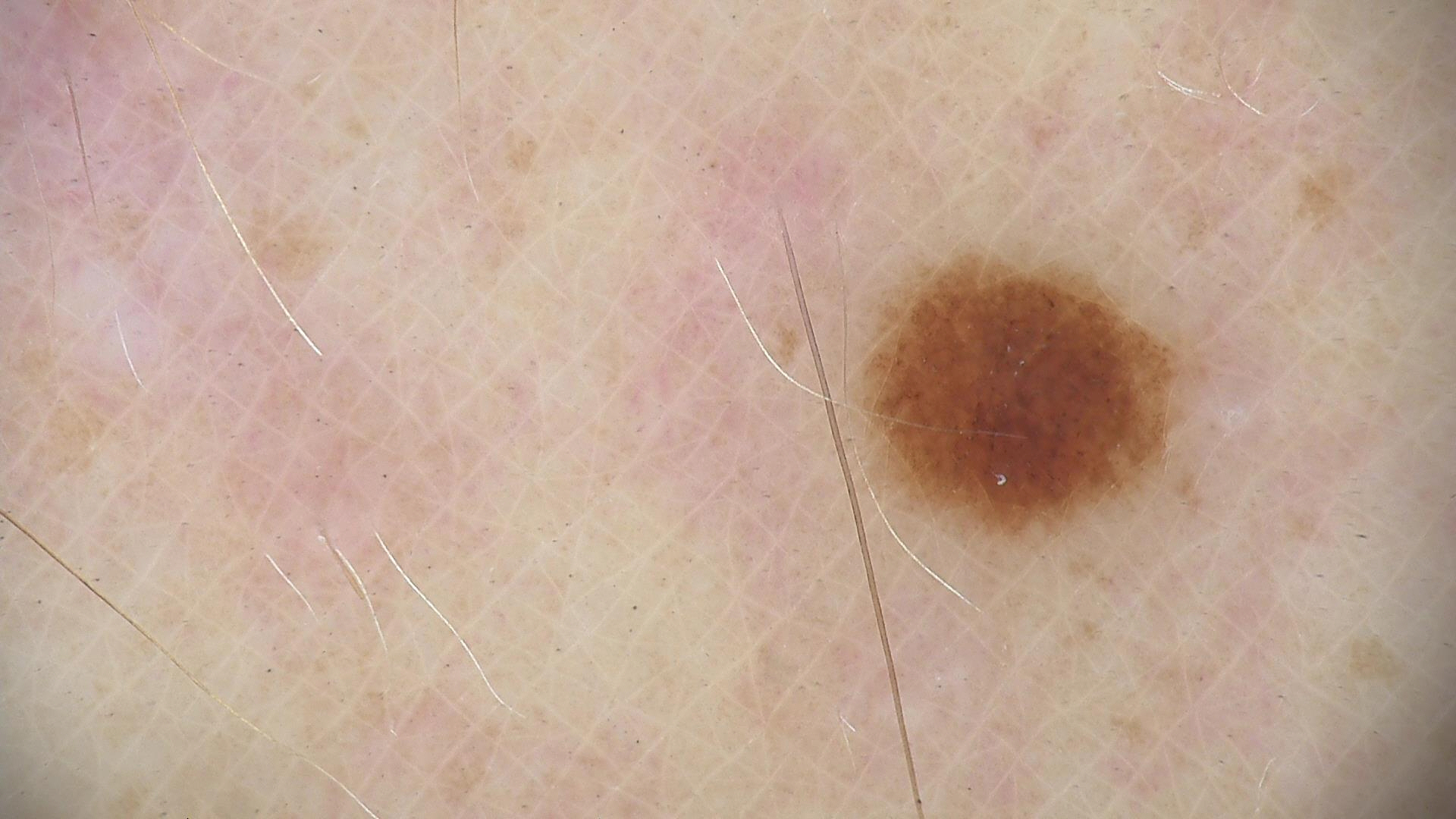A dermatoscopic image of a skin lesion.
The diagnostic label was a dysplastic junctional nevus.